A skin lesion imaged with a dermatoscope.
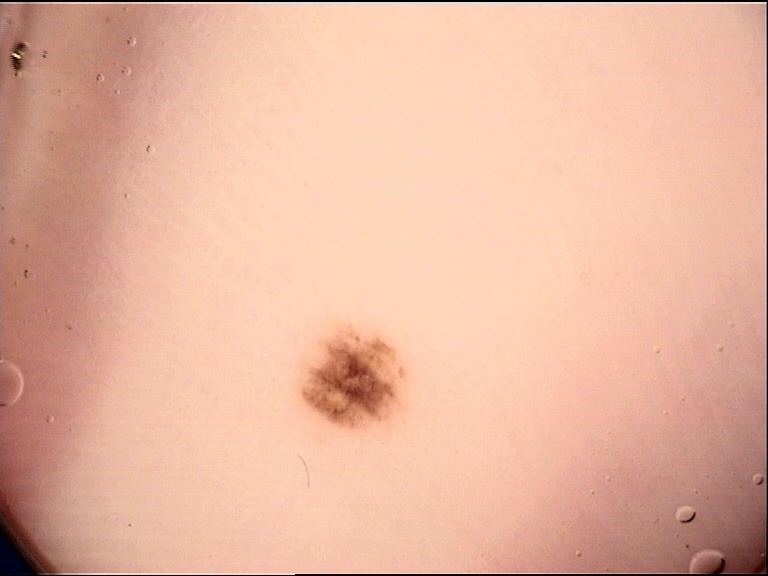Conclusion: Diagnosed as a benign lesion — an acral dysplastic junctional nevus.